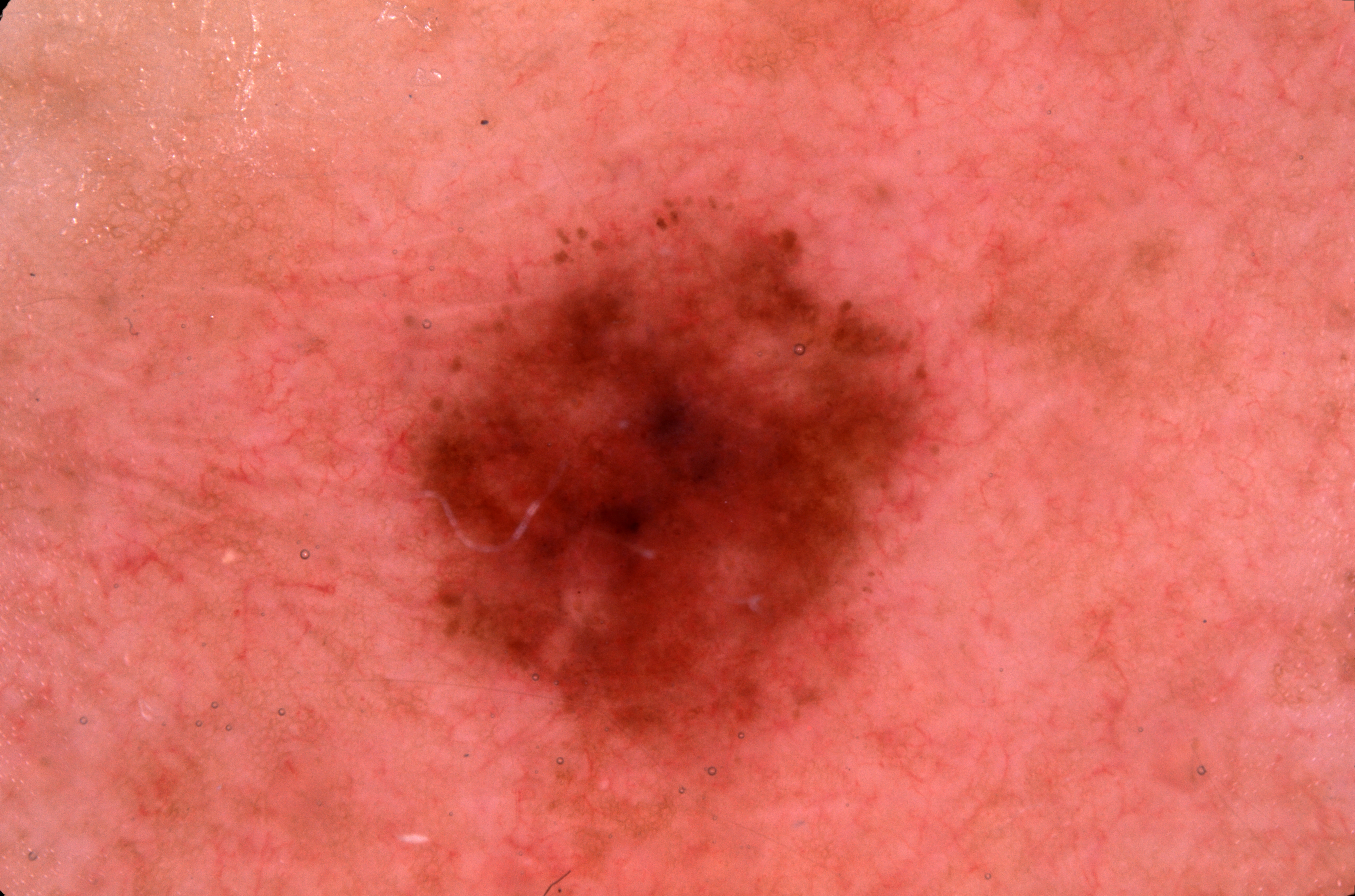The patient is a male about 40 years old. Dermoscopy of a skin lesion. The lesion covers approximately 17% of the dermoscopic field. Dermoscopic examination shows no milia-like cysts, pigment network, streaks, or negative network. The visible lesion spans left=402, top=203, right=942, bottom=770. The clinical diagnosis was a melanocytic nevus, a benign skin lesion.